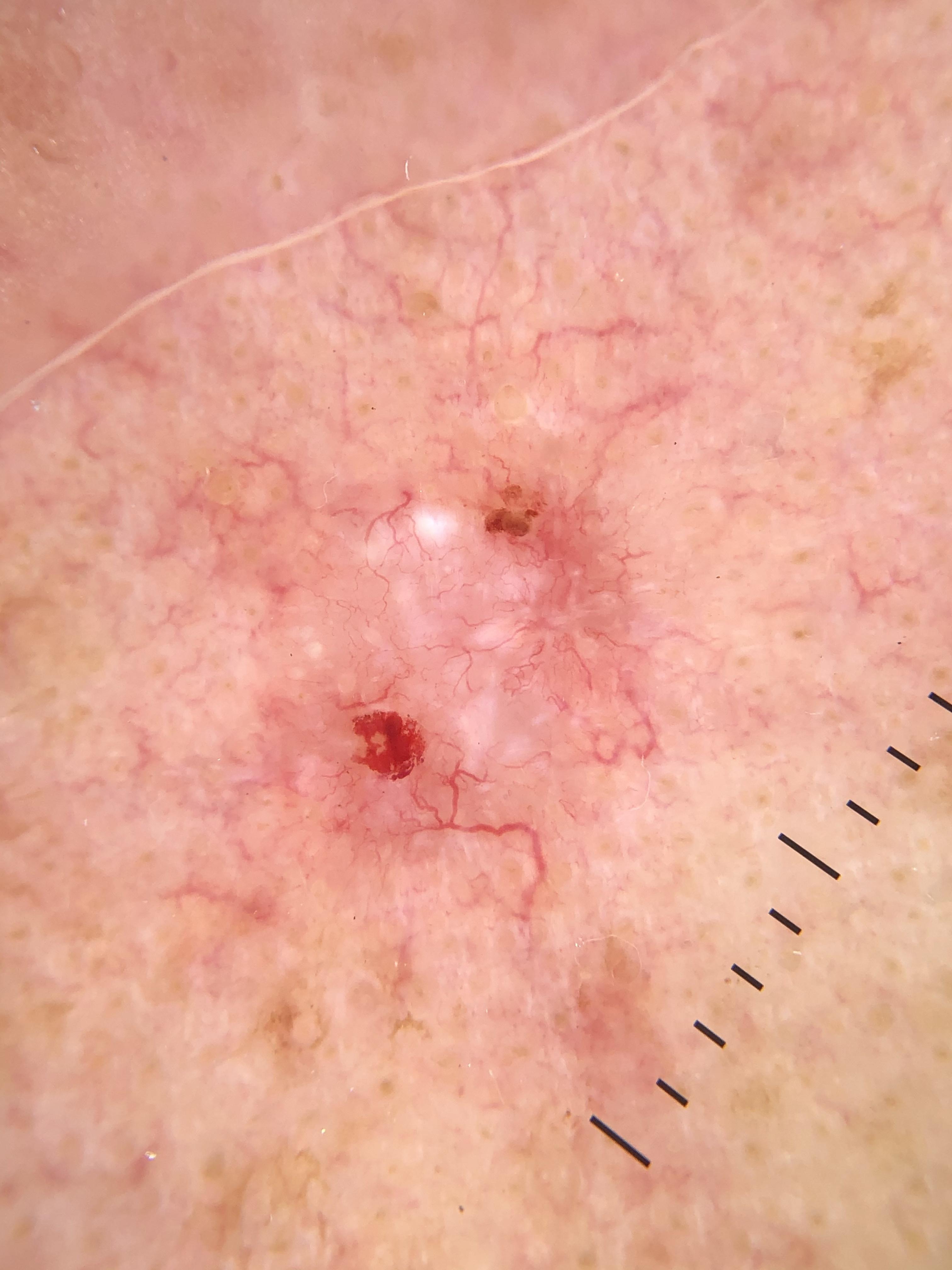Case:
• image: dermatoscopic image
• body site: the head or neck
• pathology: Basal cell carcinoma (biopsy-proven)